The patient considered this a rash, lay graders estimated MST 2 or 4, this image was taken at a distance, the leg is involved, no constitutional symptoms were reported — 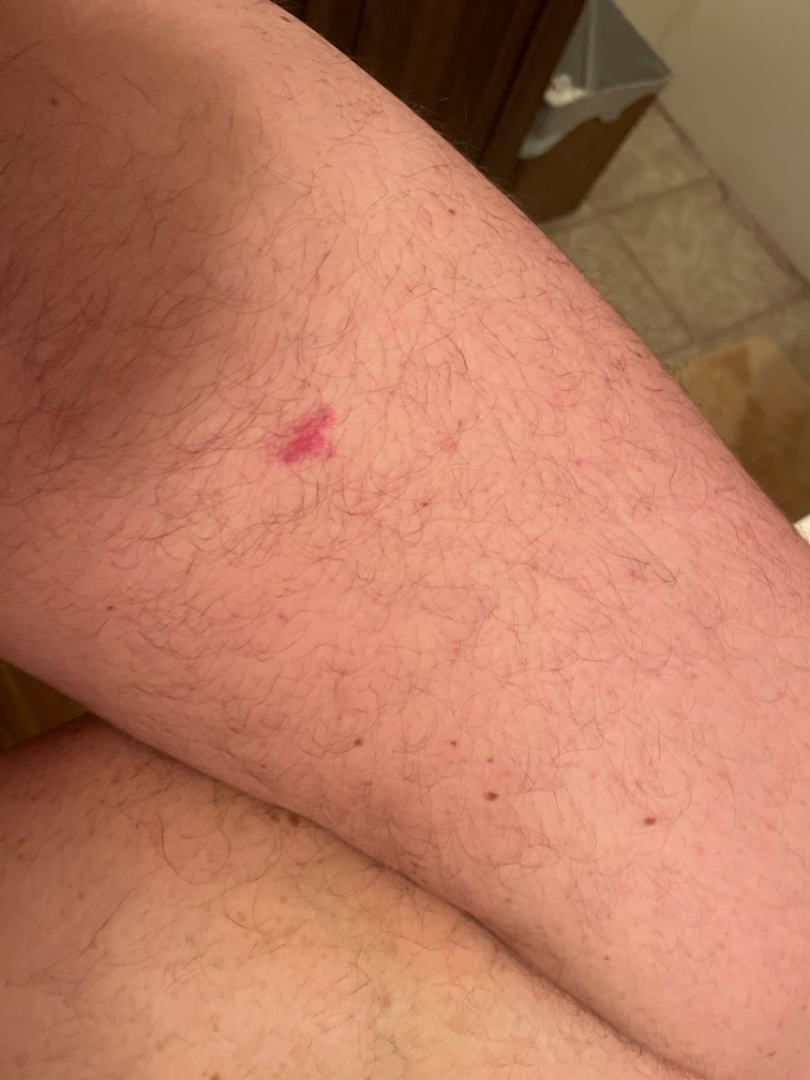{"differential": {"tied_lead": ["Allergic Contact Dermatitis", "Basal Cell Carcinoma"]}}